A dermoscopy image of a single skin lesion:
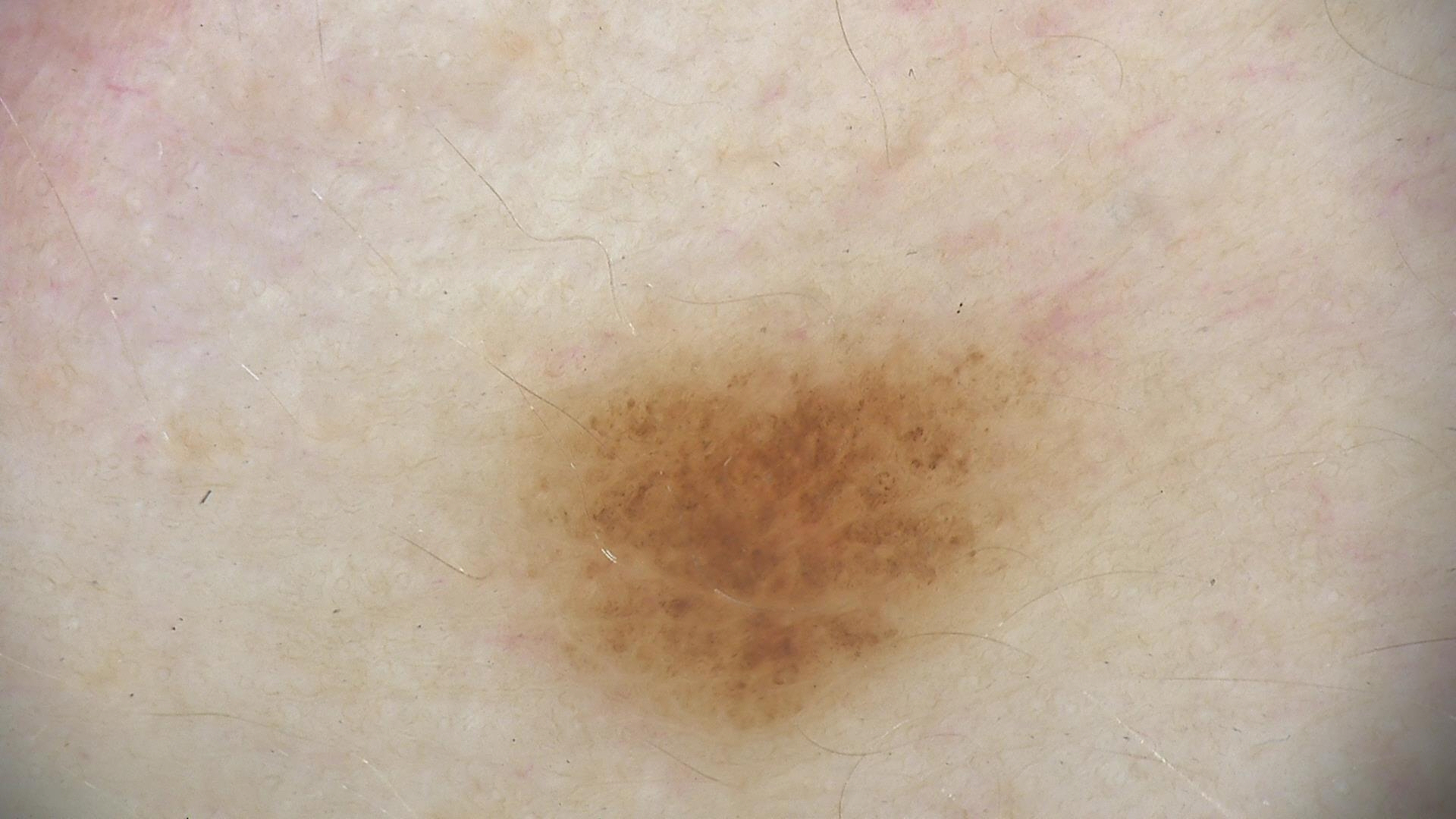class: dysplastic junctional nevus (expert consensus).